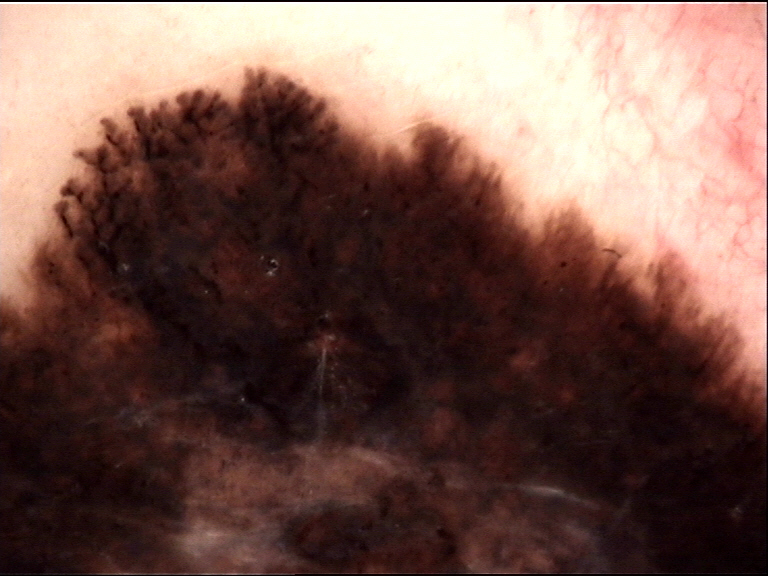Q: What is the imaging modality?
A: dermatoscopy
Q: What did the workup show?
A: melanoma (biopsy-proven)